A skin lesion imaged with a dermatoscope; a female subject in their mid-60s: 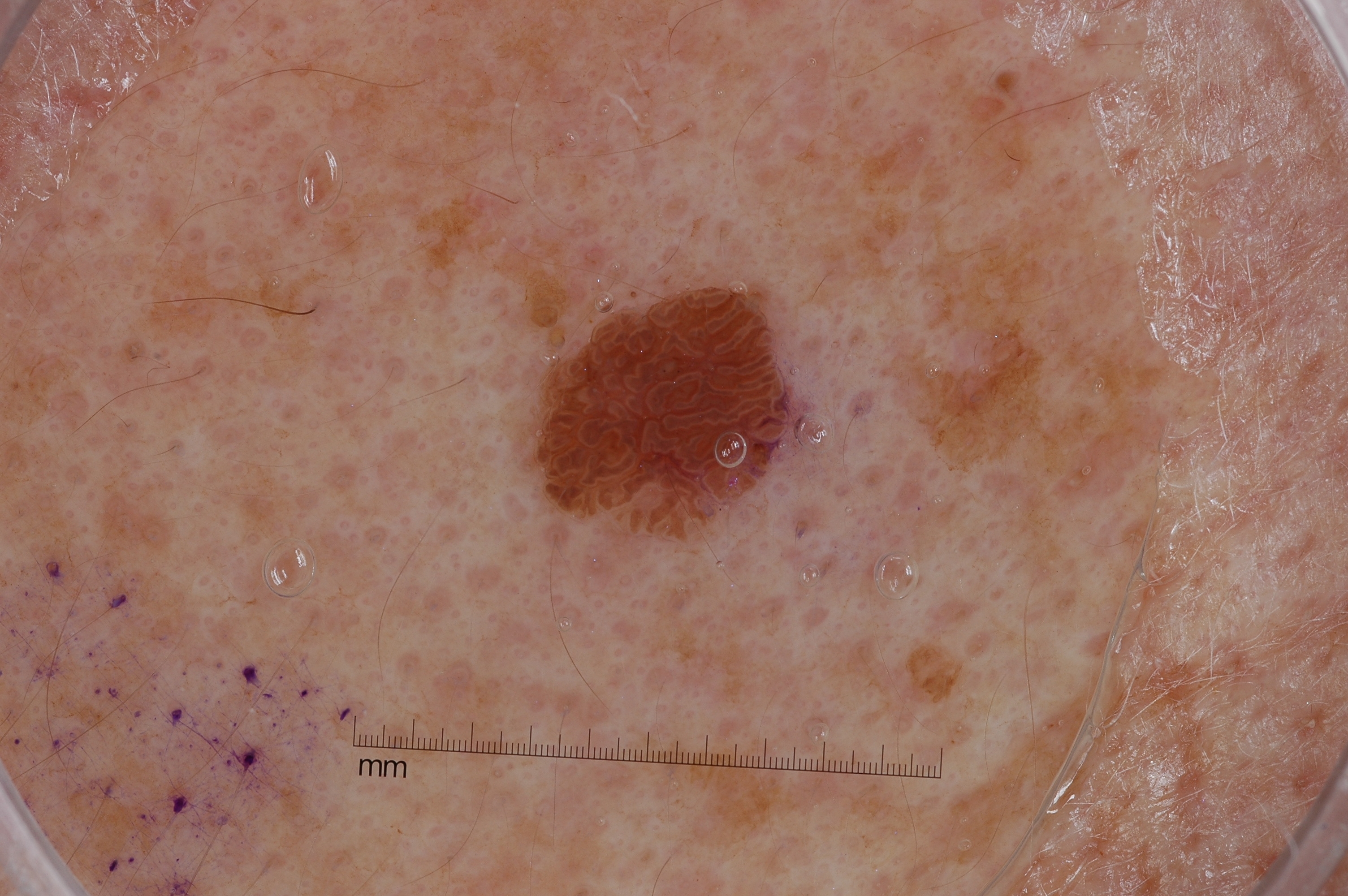absent dermoscopic findings: milia-like cysts, pigment network, streaks, and negative network; location: 537 287 779 532; lesion extent: ~4% of the field; assessment: a seborrheic keratosis, a benign skin lesion.